The photograph is a close-up of the affected area:
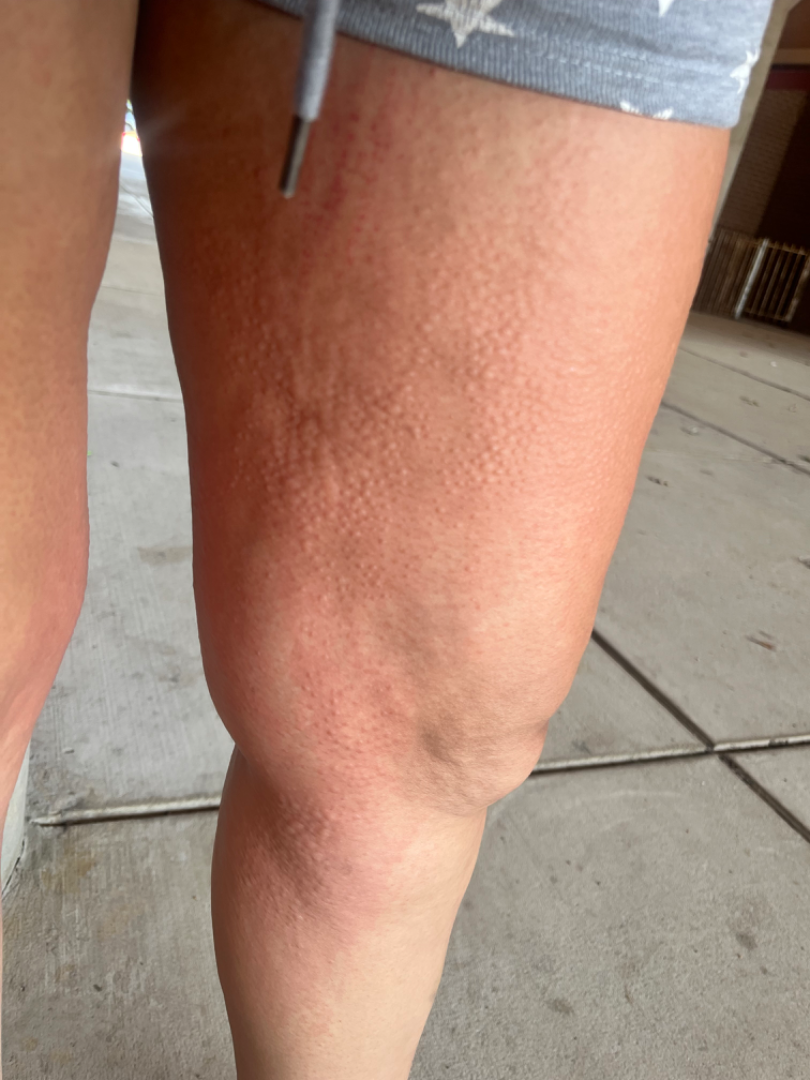{"assessment": "ungradable on photographic review"}